A clinical photograph showing a skin lesion in context; the patient is Fitzpatrick skin type II; a female subject aged 48 to 52.
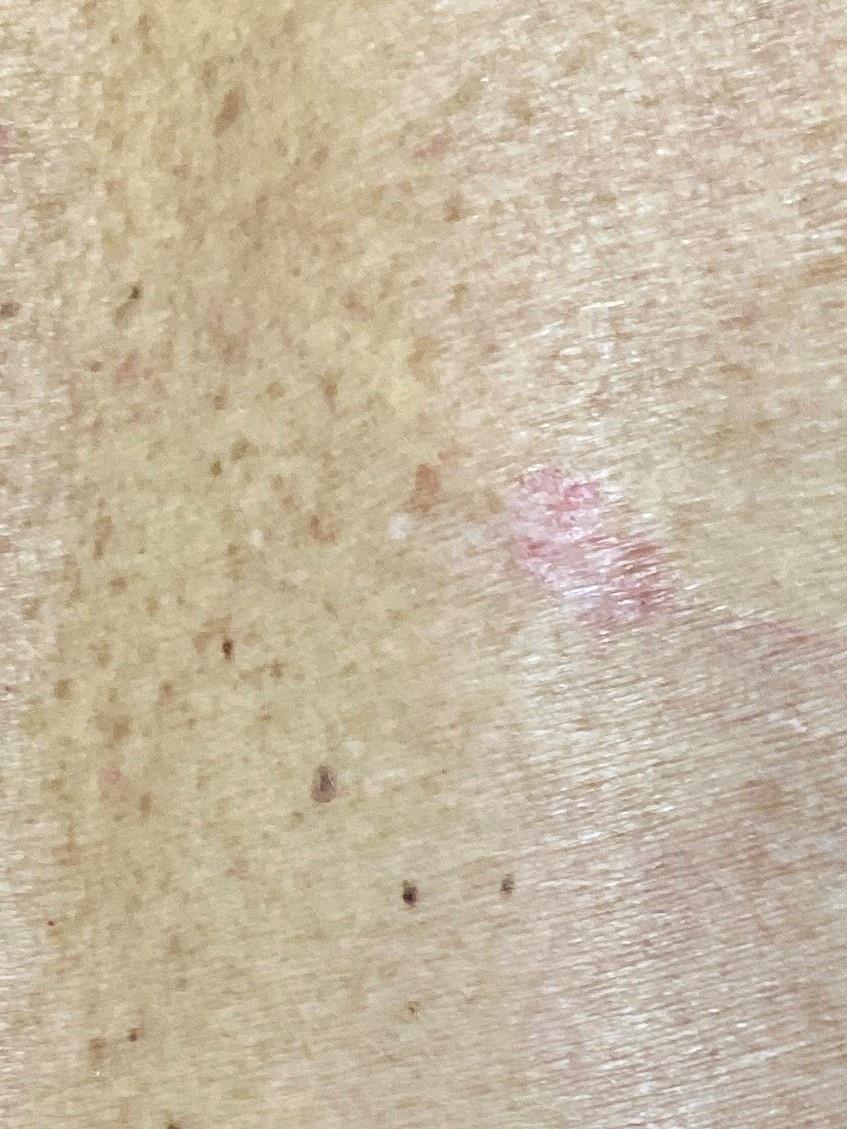The lesion is on the trunk. Confirmed on histopathology as a basal cell carcinoma.